A dermatoscopic image of a skin lesion: 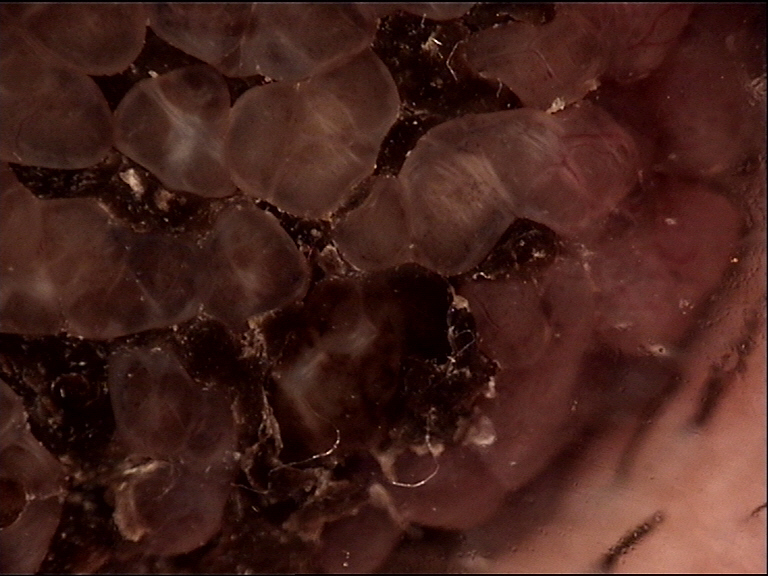– assessment: congenital compound nevus (expert consensus)